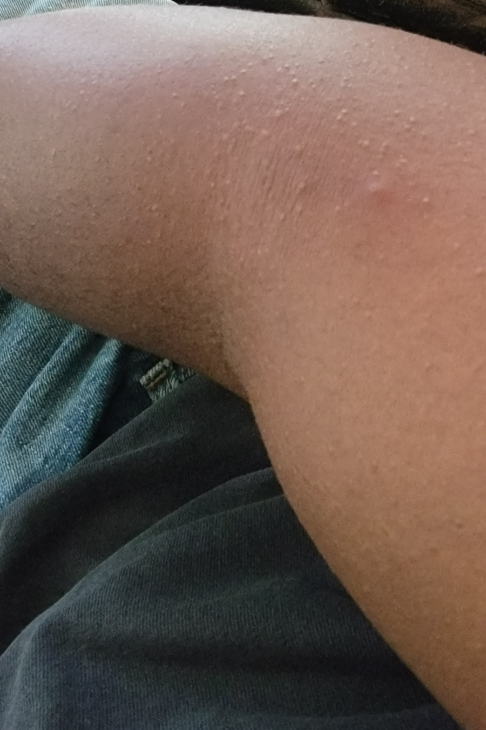Notes:
• impression · Lichen nitidus (possible); Eczema (possible); Insect Bite (possible)